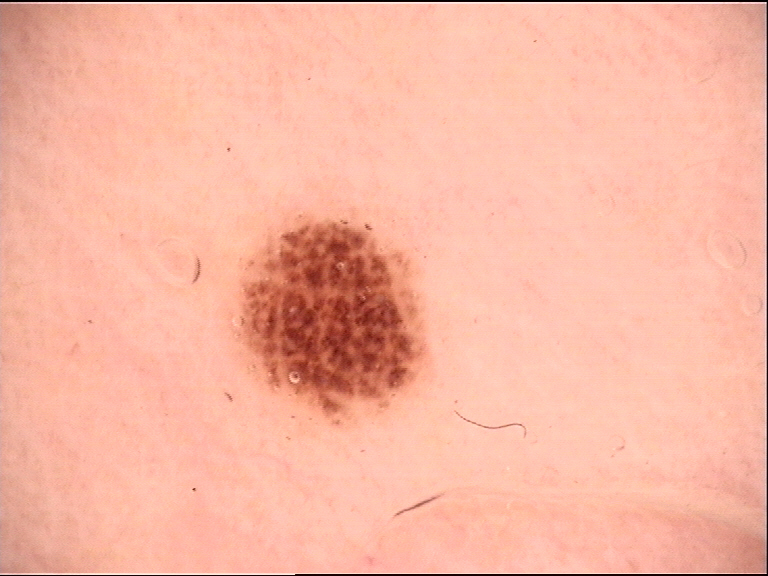<lesion>
  <image>dermoscopy</image>
  <lesion_type>
    <main_class>banal</main_class>
    <pattern>compound</pattern>
  </lesion_type>
  <diagnosis>
    <name>compound nevus</name>
    <code>cb</code>
    <malignancy>benign</malignancy>
    <super_class>melanocytic</super_class>
    <confirmation>expert consensus</confirmation>
  </diagnosis>
</lesion>